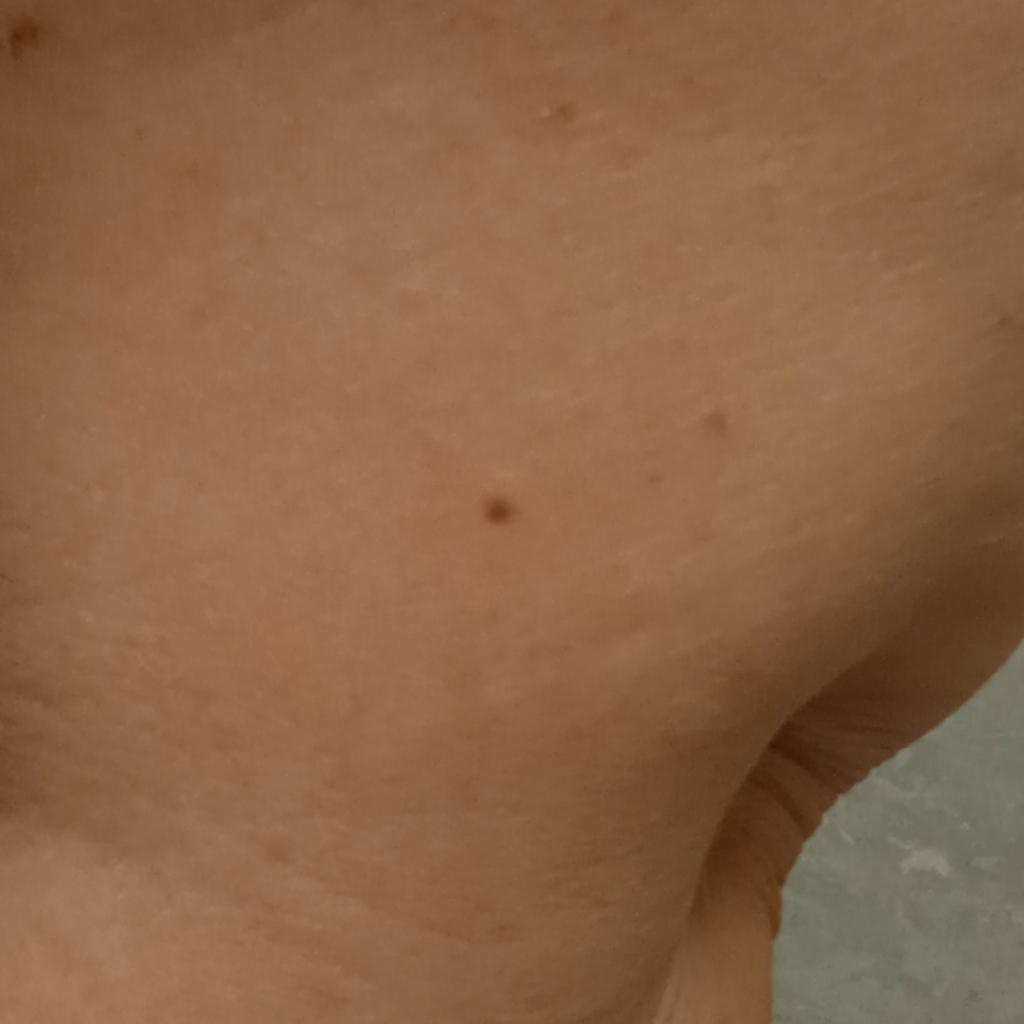Dermatologist review favored a melanocytic nevus.